A close-up photograph, the patient indicates the lesion is raised or bumpy, the arm is involved, reported lesion symptoms include bothersome appearance.
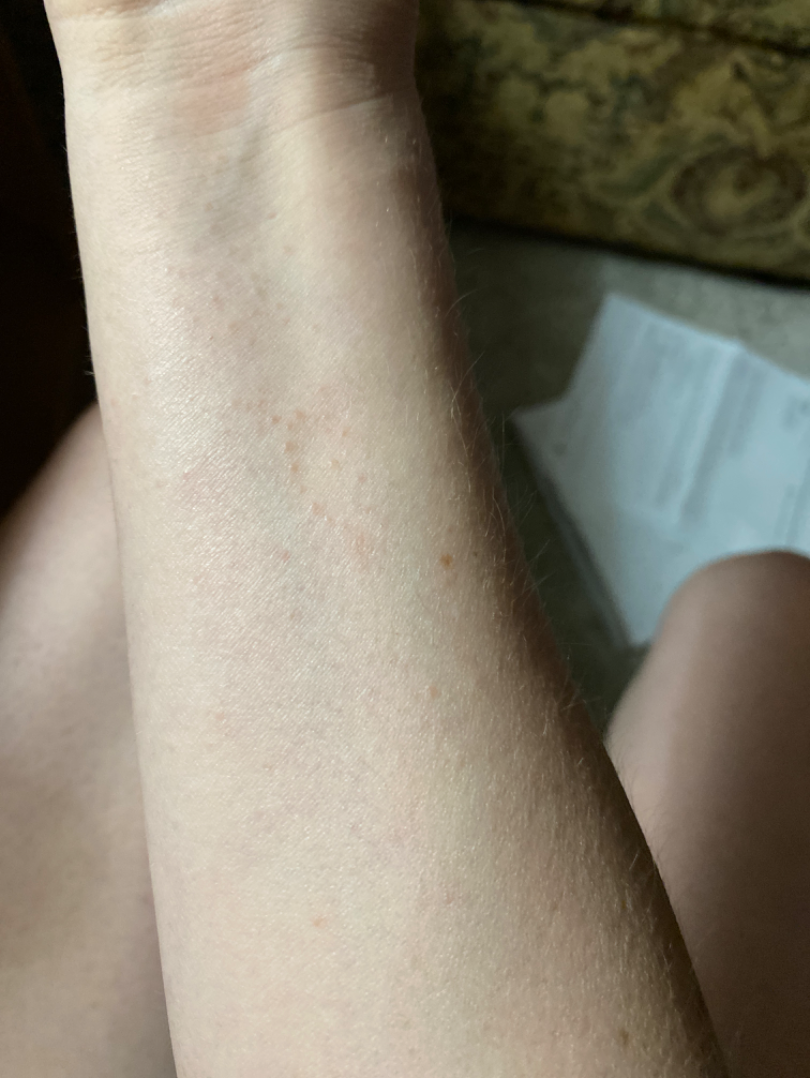Review: The case was difficult to assess from the available photograph.